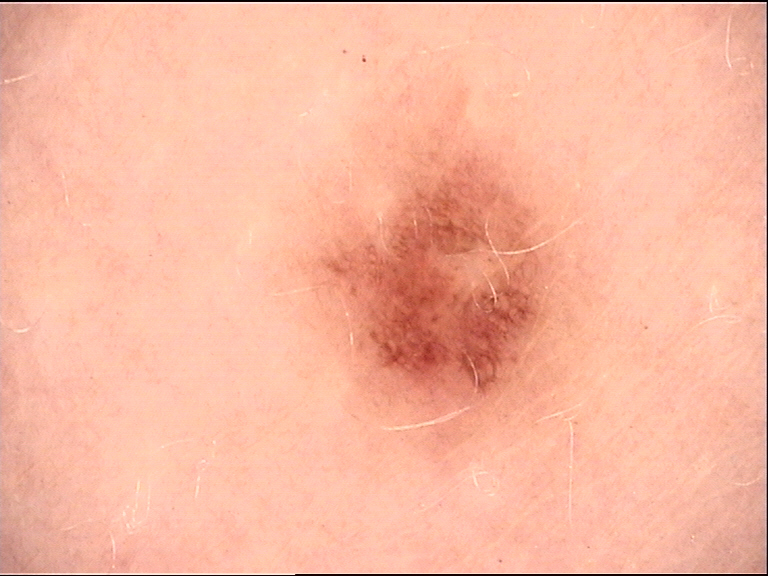A dermatoscopic image of a skin lesion. Labeled as a dysplastic junctional nevus.